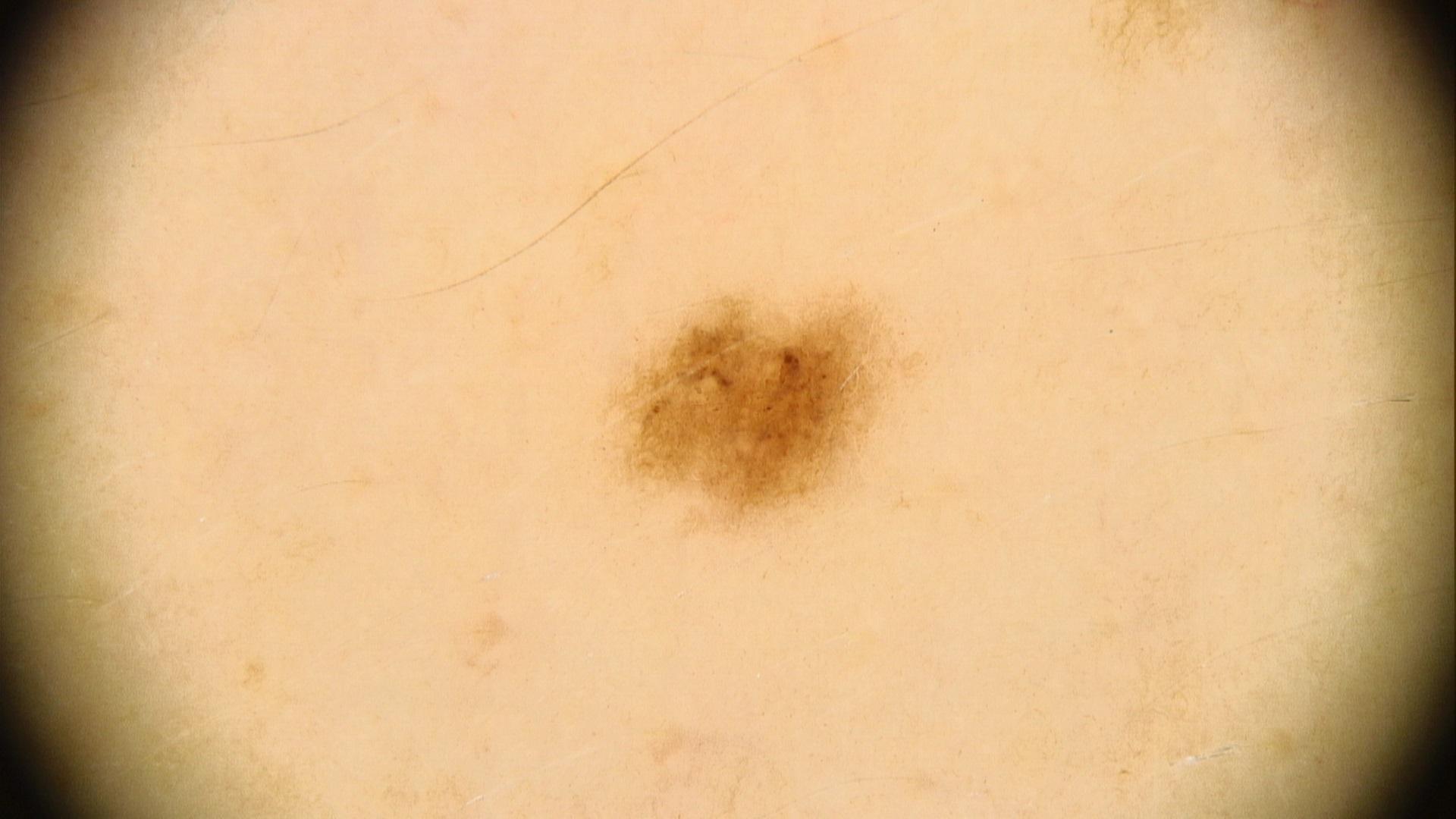  diagnosis:
    name: Nevus
    malignancy: benign
    confirmation: expert clinical impression
    lineage: melanocytic